A dermatoscopic image of a skin lesion. A female patient aged 58 to 62:
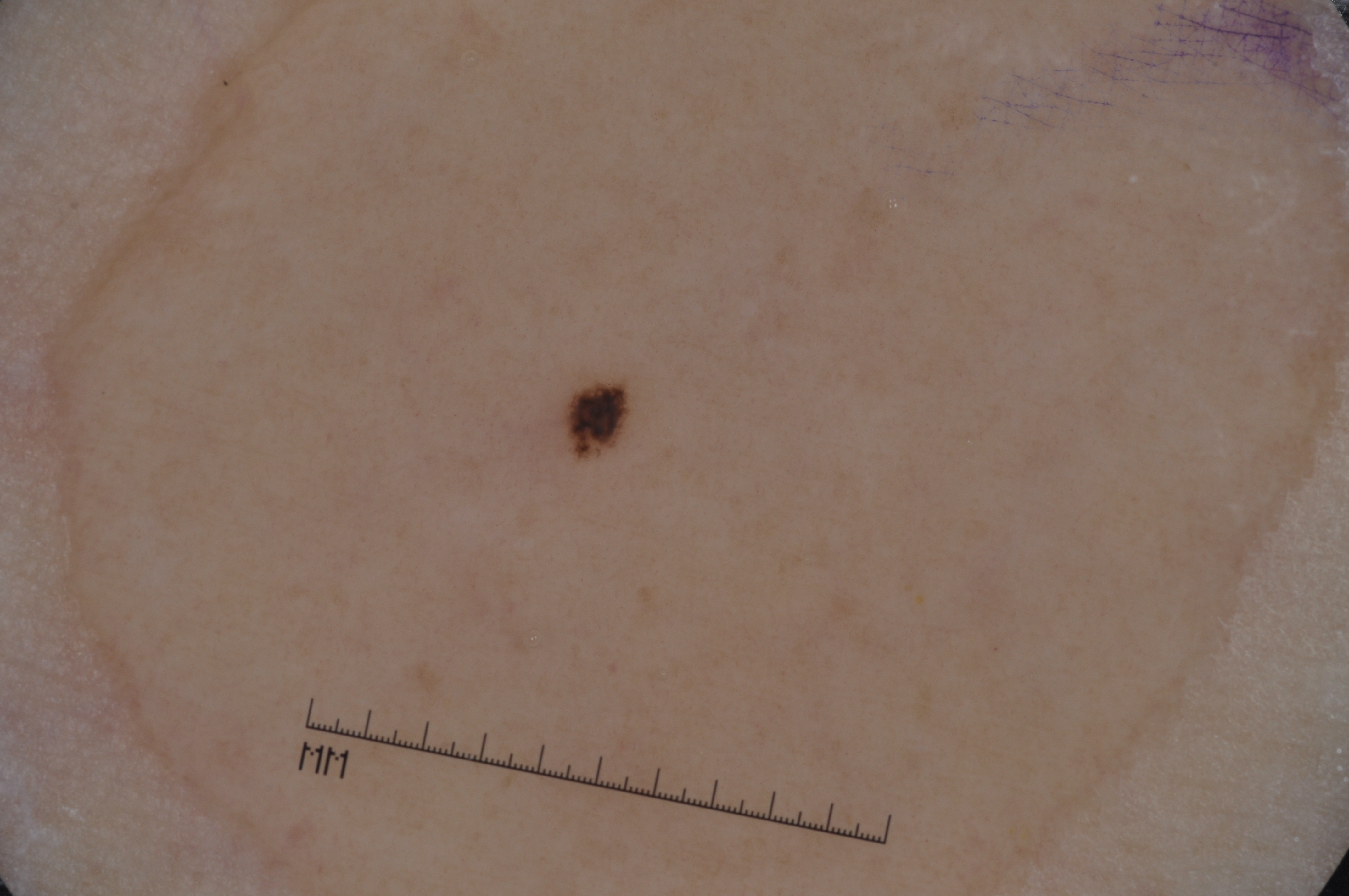Lesion location: x1=548, y1=365, x2=643, y2=455. Dermoscopic examination shows pigment network, with no negative network, streaks, or milia-like cysts. The diagnostic assessment was a melanocytic nevus.